The subject is 50–59, male. An image taken at a distance. The affected area is the back of the hand — 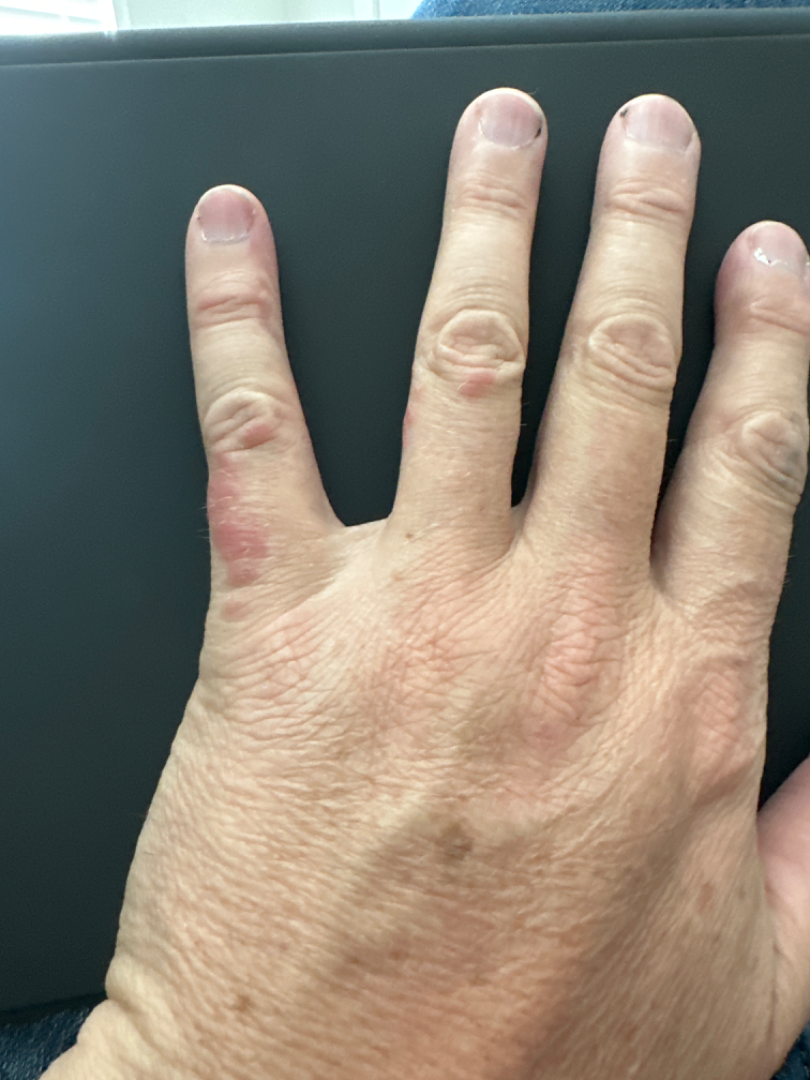patient describes the issue as: a rash
present for: less than one week
described texture: raised or bumpy
lesion symptoms: itching
differential: Eczema and Allergic Contact Dermatitis were considered with similar weight; less probable is Scabies